An image taken at a distance.
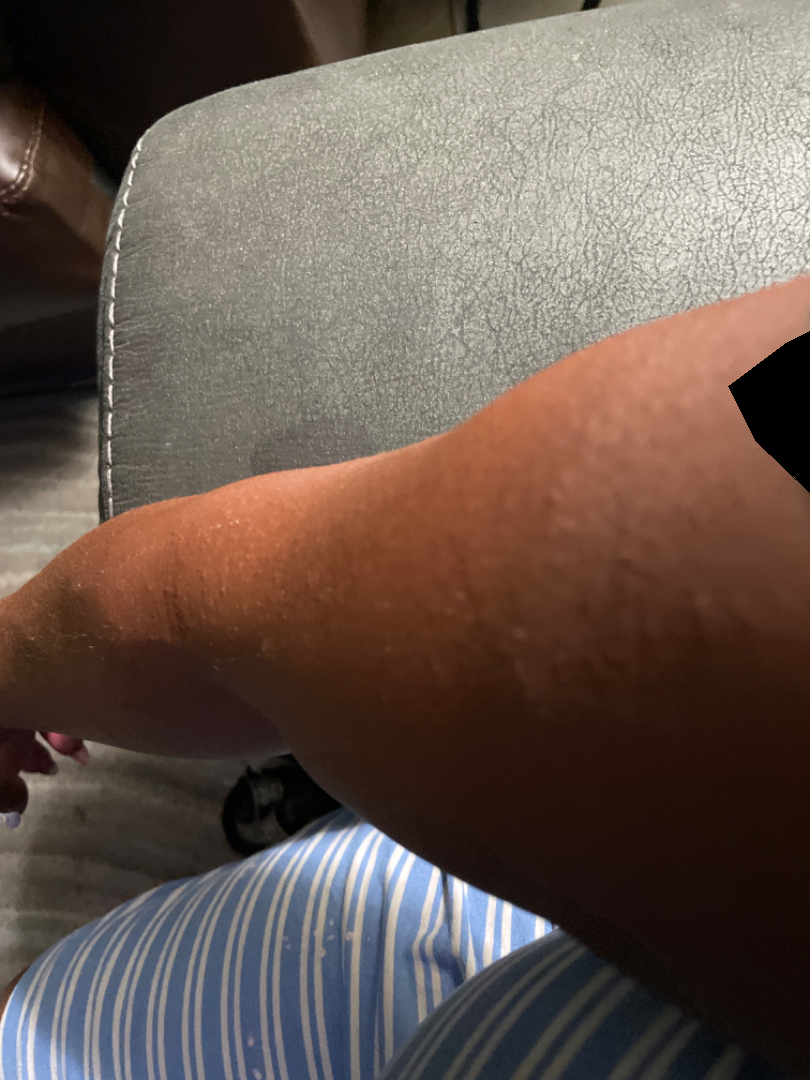assessment — not assessable